A dermoscopic photograph of a skin lesion.
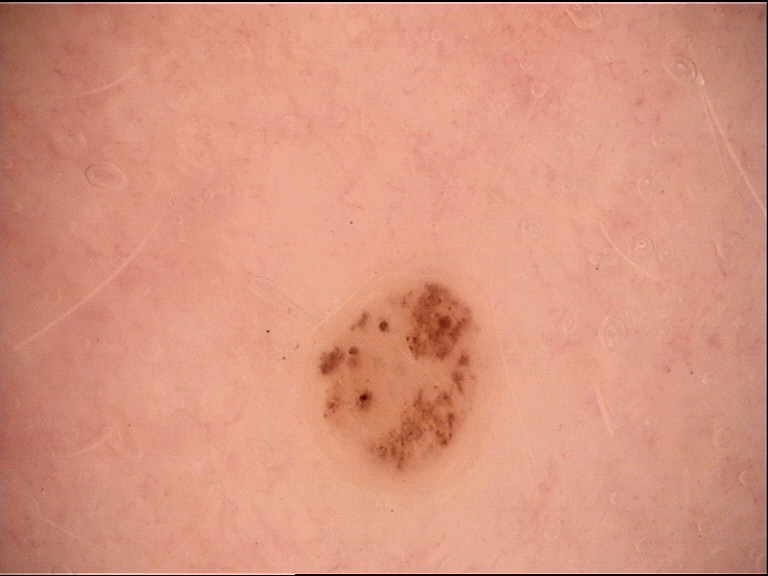category: banal; diagnosis: dermal nevus (expert consensus).